A dermoscopic close-up of a skin lesion.
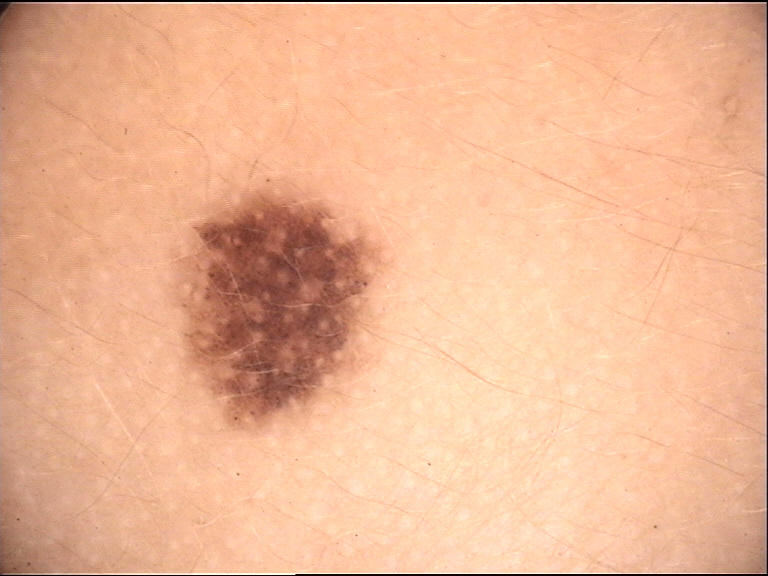{
  "diagnosis": {
    "name": "congenital junctional nevus",
    "code": "cjb",
    "malignancy": "benign",
    "super_class": "melanocytic",
    "confirmation": "expert consensus"
  }
}